An image taken at an angle. The affected area is the leg: 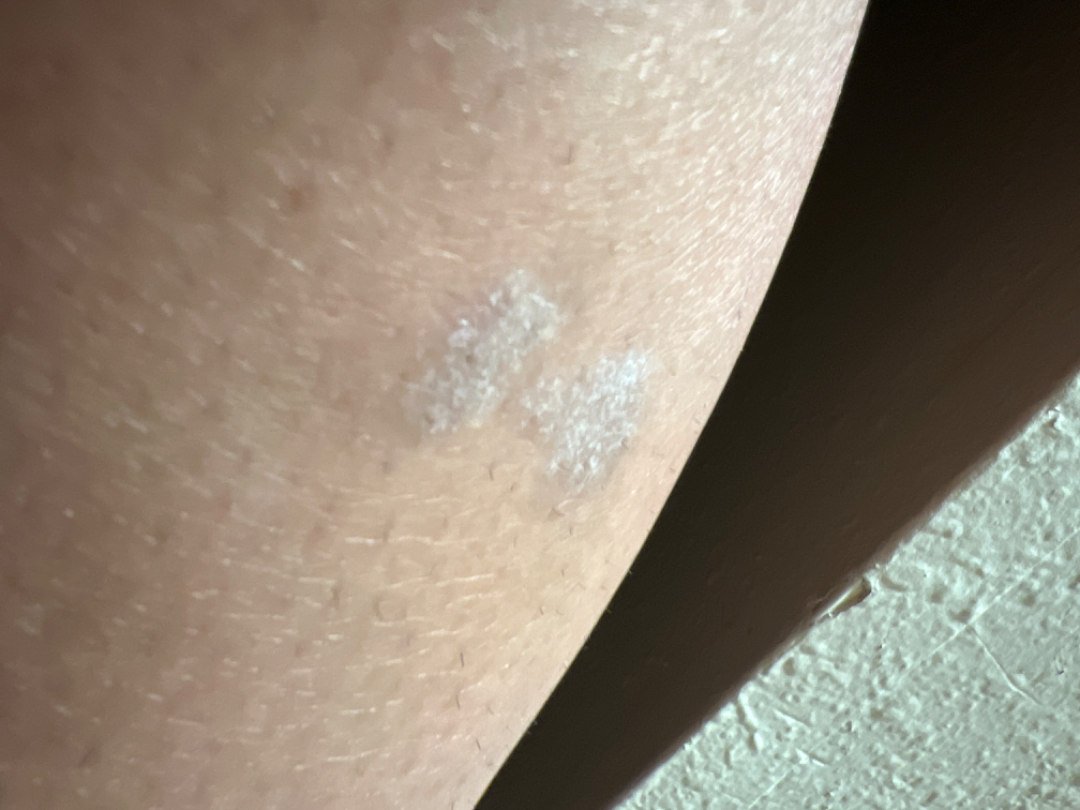On photographic review by a dermatologist, the impression is Lichen planus/lichenoid eruption.